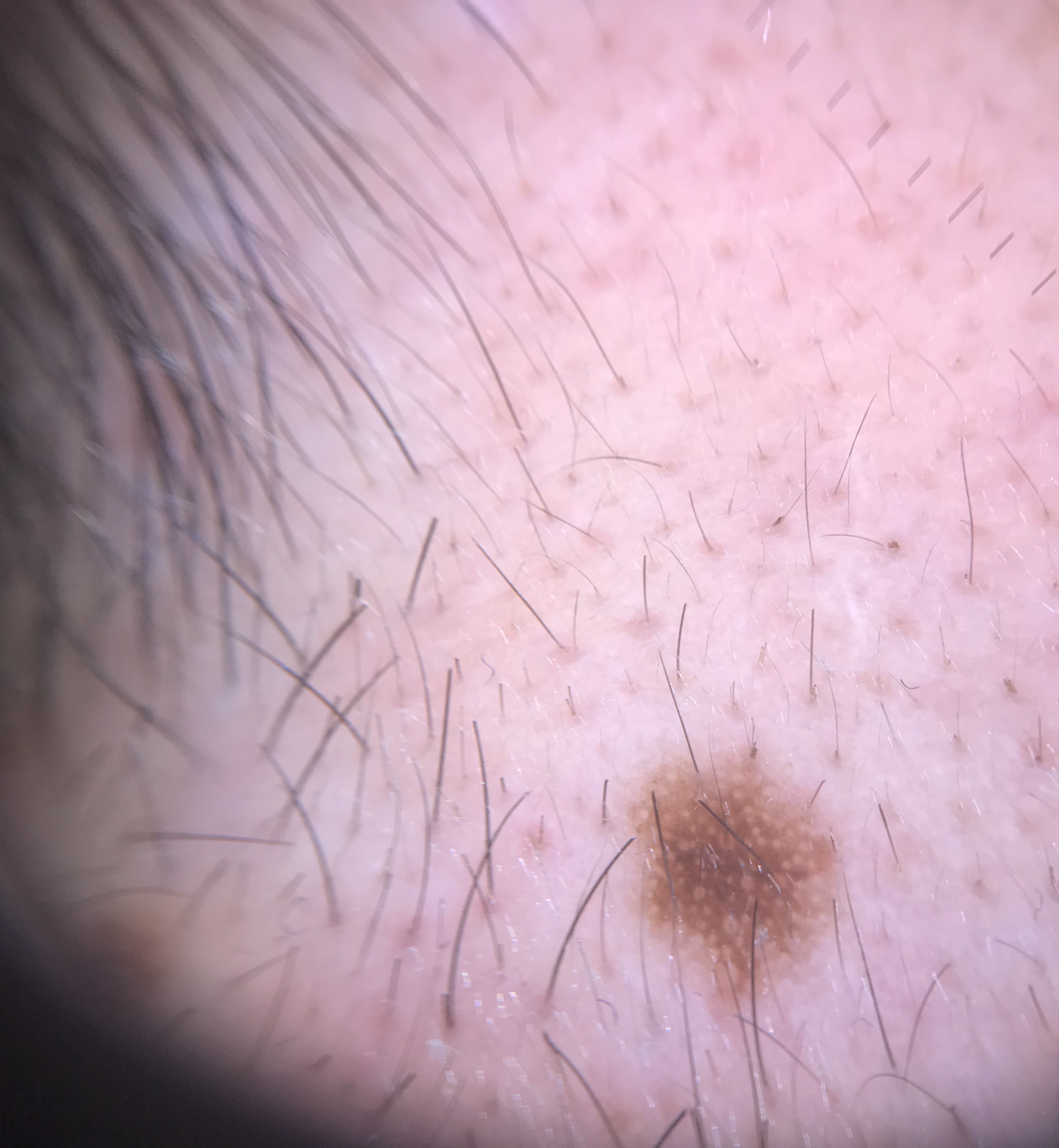Consistent with a Miescher nevus.